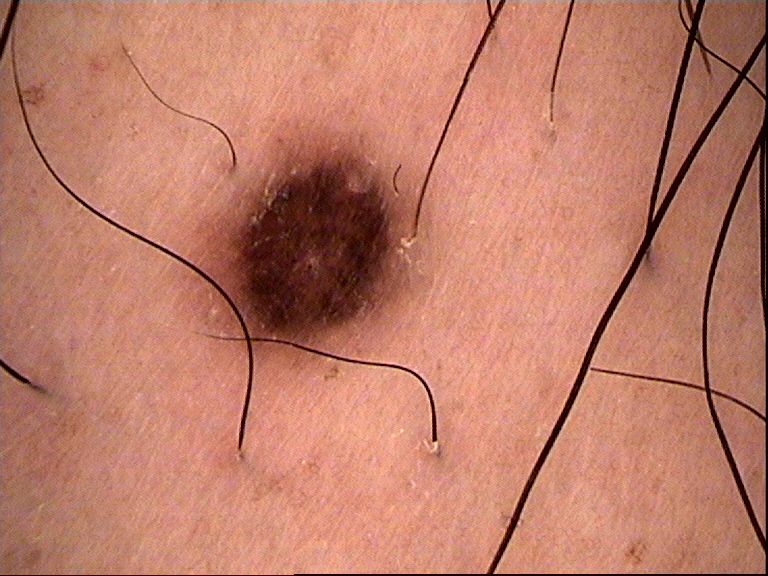A dermoscopic close-up of a skin lesion. Consistent with a benign lesion — a dysplastic junctional nevus.